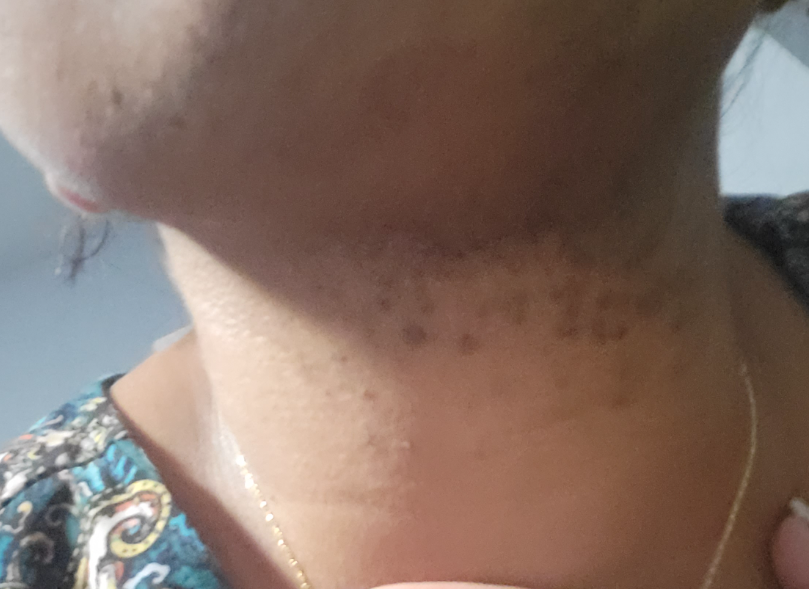{
  "patient": "female, age 40–49",
  "texture": "raised or bumpy",
  "duration": "more than five years",
  "skin_tone": {
    "monk_skin_tone": [
      3,
      5
    ]
  },
  "body_site": "head or neck",
  "shot_type": "at an angle",
  "patient_category": "a hair problem",
  "differential": {
    "tied_lead": [
      "Acne",
      "Folliculitis"
    ]
  }
}